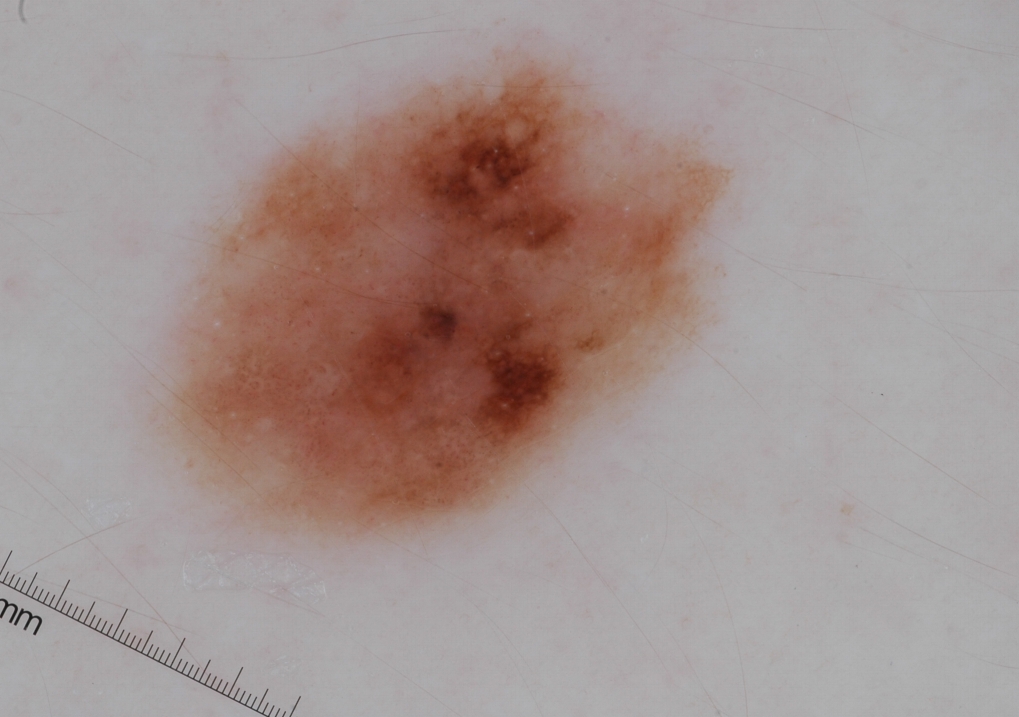| feature | finding |
|---|---|
| image type | dermatoscopic image of a skin lesion |
| dermoscopic features | globules, milia-like cysts, and negative network; absent: pigment network and streaks |
| location | (167, 52, 730, 539) |
| diagnosis | a melanocytic nevus, a benign lesion |